A female patient 20 years of age · collected as part of a research study, without a referral diagnosis · the patient says their skin reddens with sun exposure · a moderate number of moles by the patient's own estimate · on a questionnaire the patient reported no prior organ transplant and no family history of skin cancer · a clinical photograph showing a skin lesion: 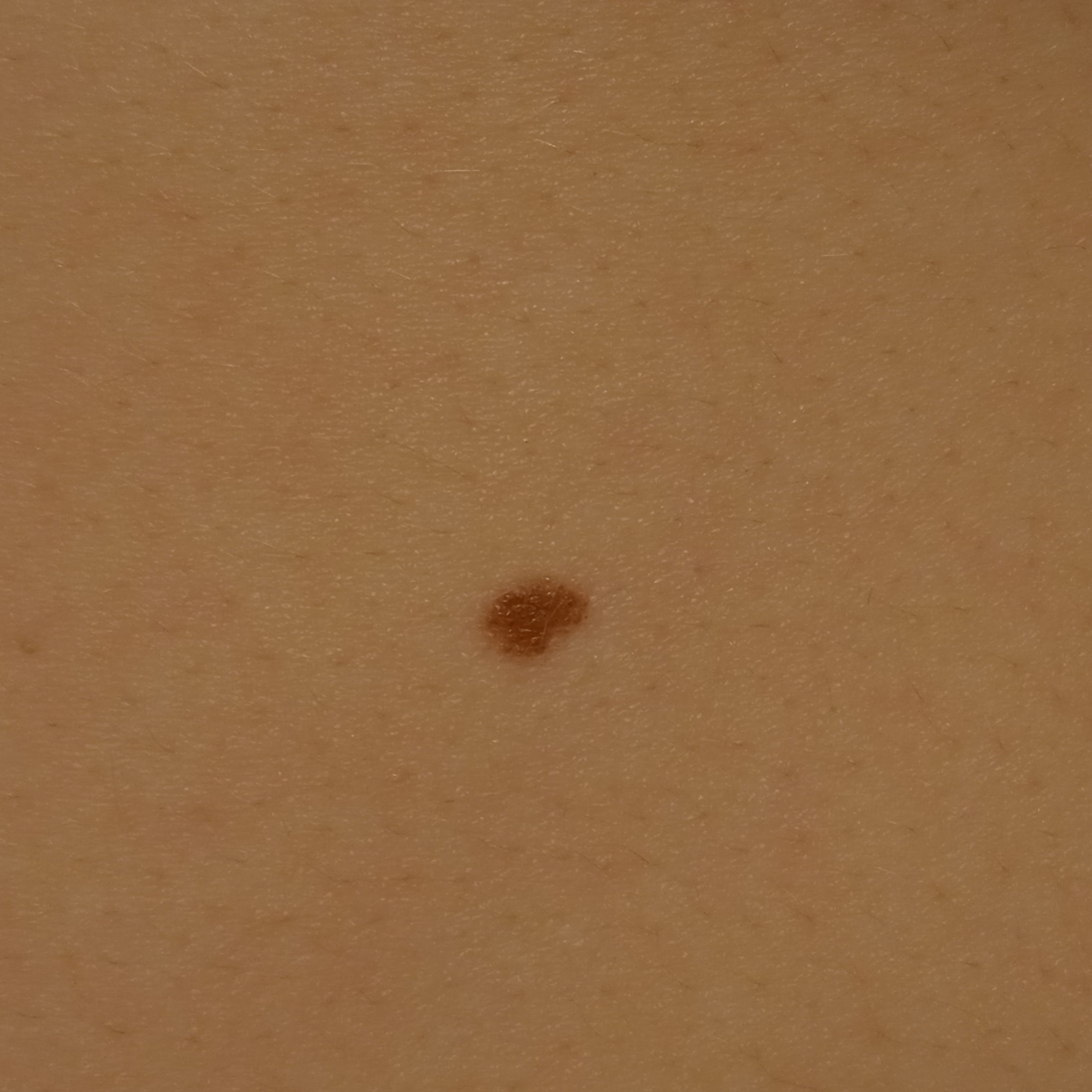The lesion involves the torso. Dermatologist review favored a melanocytic nevus.